Dermoscopy of a skin lesion: 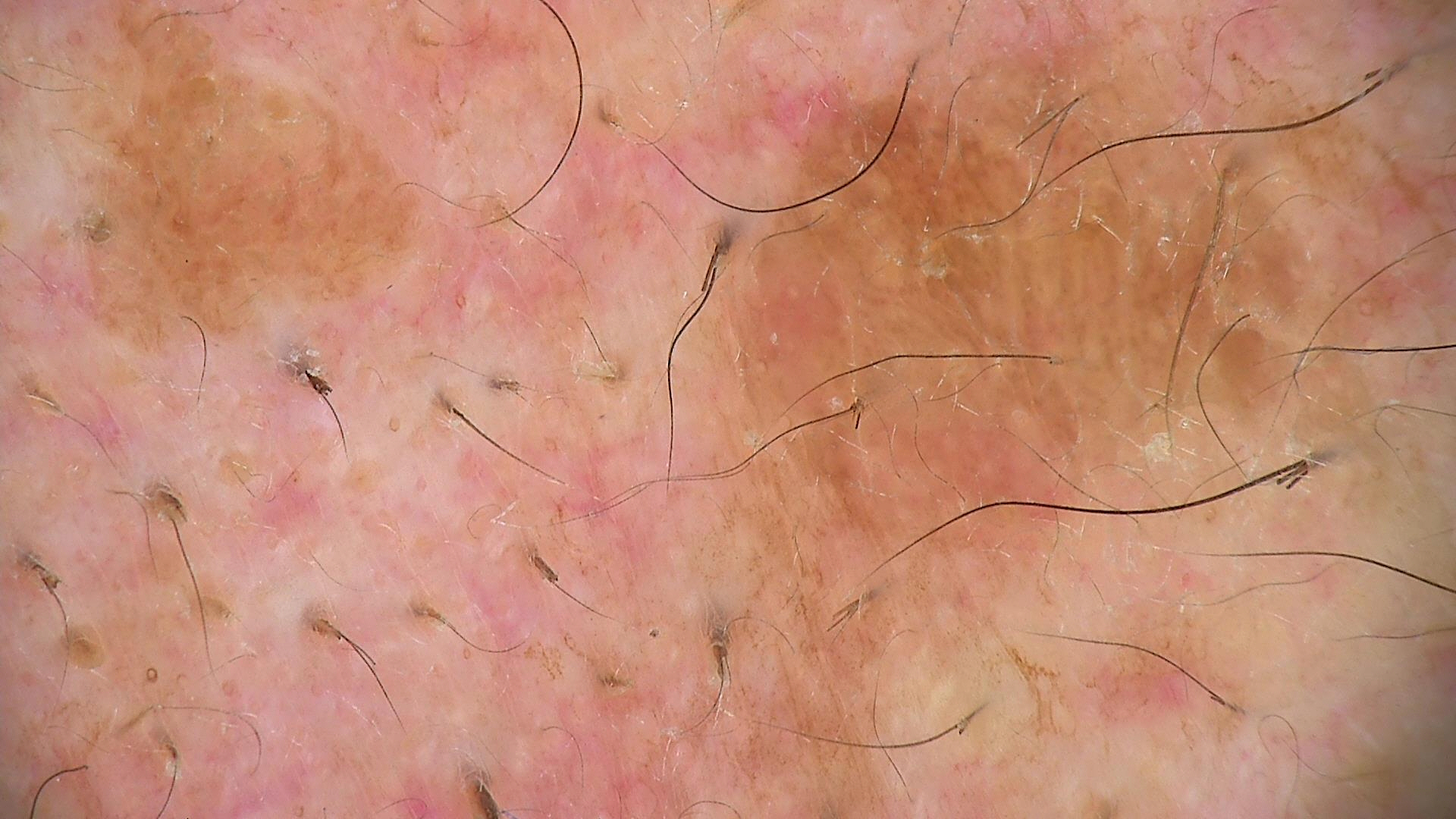Labeled as a benign, keratinocytic lesion — a seborrheic keratosis.